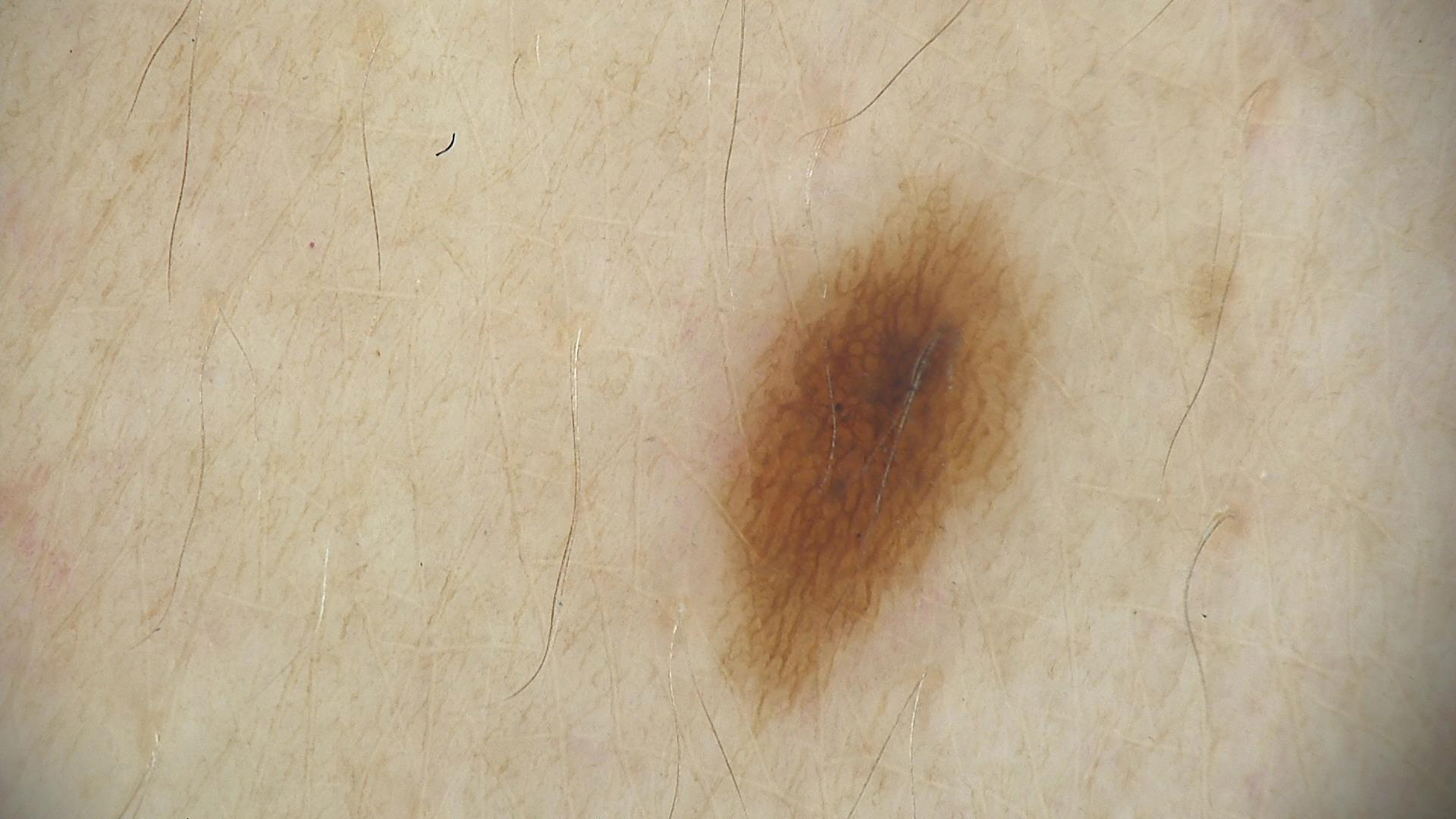Q: What is the imaging modality?
A: dermatoscopy
Q: What is the diagnosis?
A: dysplastic junctional nevus (expert consensus)